A dermoscopic image of a skin lesion: 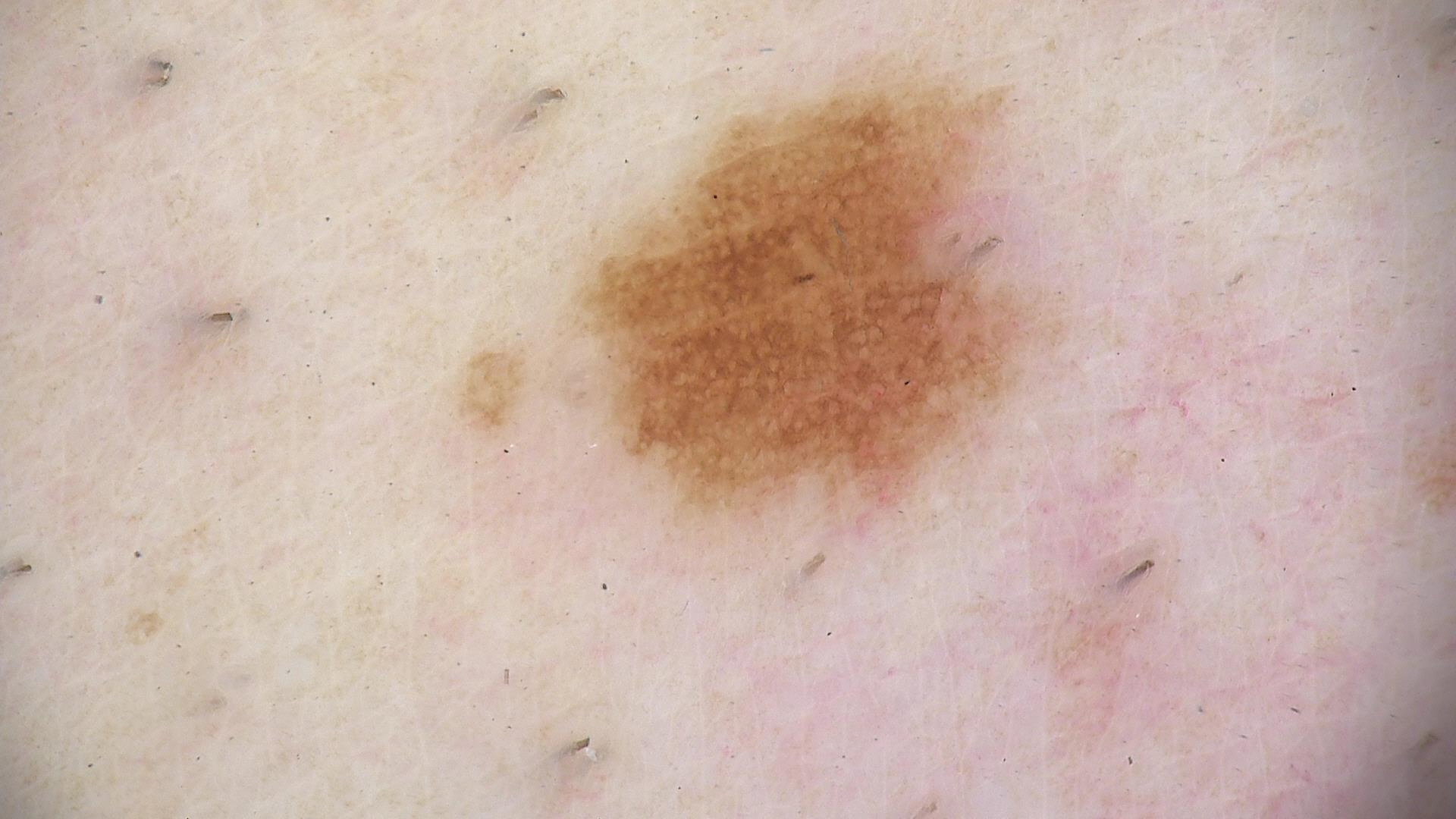| key | value |
|---|---|
| diagnosis | dysplastic junctional nevus (expert consensus) |